A skin lesion imaged with a dermatoscope.
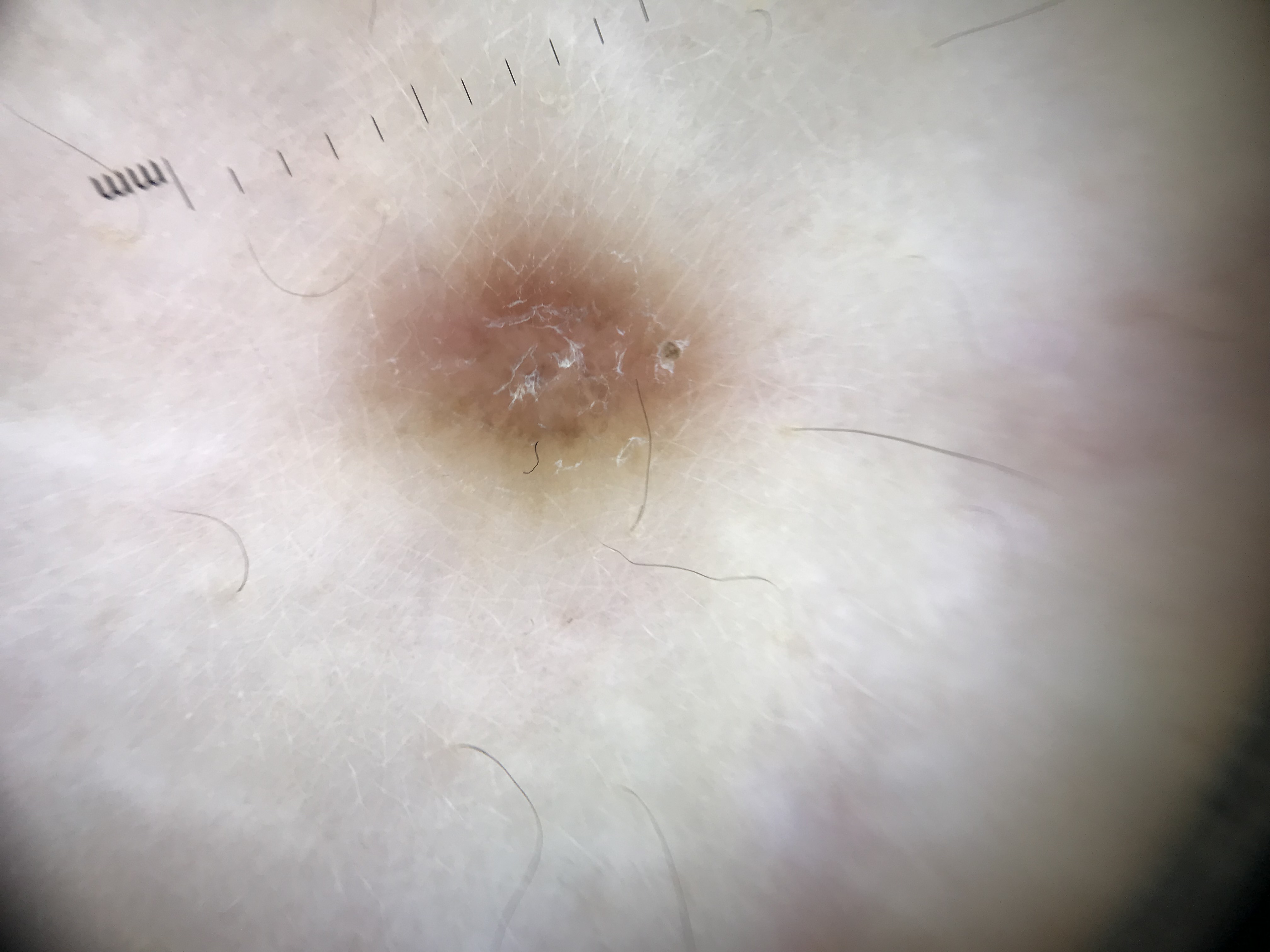The morphology is that of a fibro-histiocytic lesion. Diagnosed as a dermatofibroma.